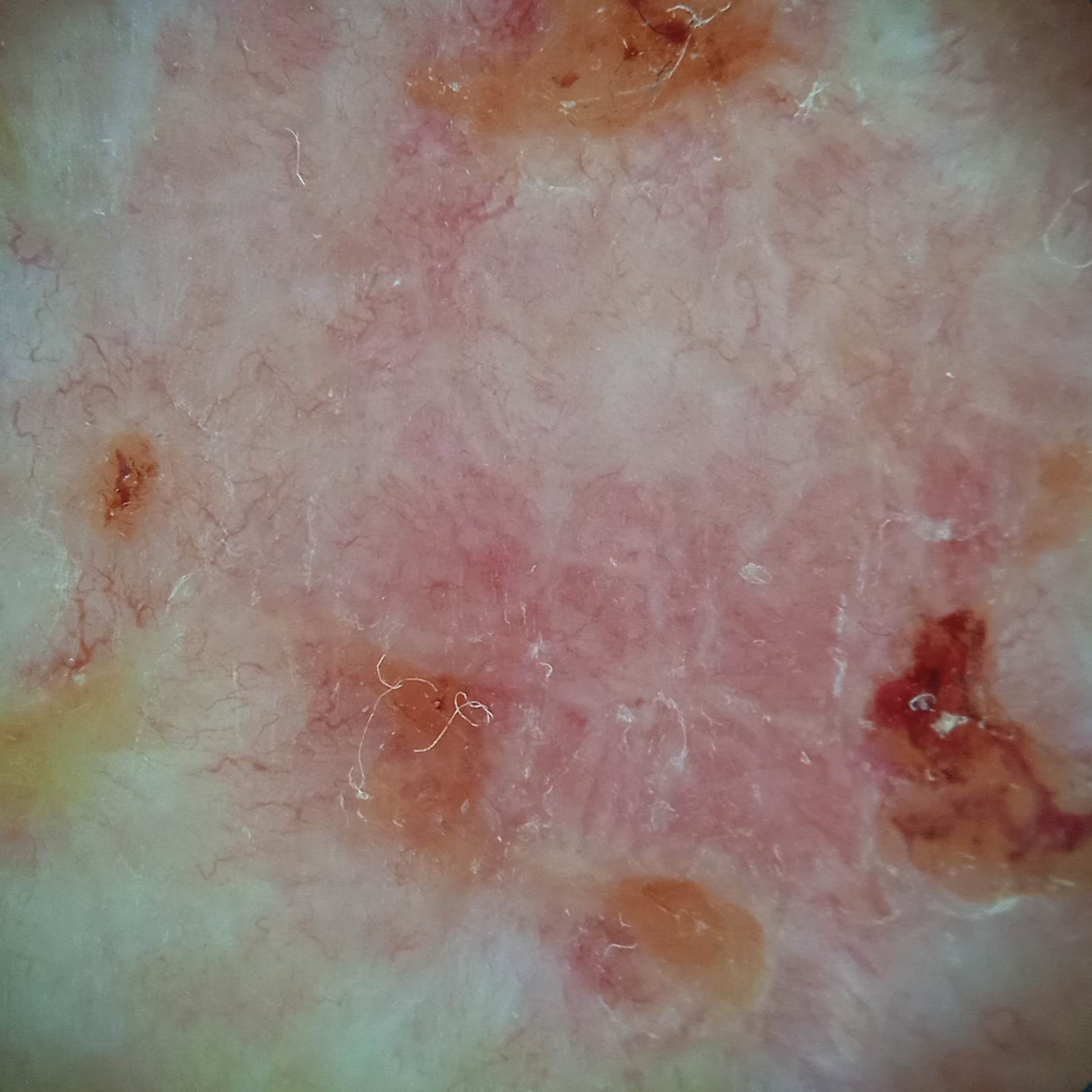mole_burden: few melanocytic nevi overall
risk_factors:
  positive:
    - a personal history of cancer
    - a family history of skin cancer
referral: clinical suspicion of basal cell carcinoma
patient:
  age: 81
  sex: male
image: dermoscopic image
lesion_location: the back
lesion_size:
  diameter_mm: 12.6
diagnosis:
  name: basal cell carcinoma
  malignancy: malignant
  procedure: excision
  tumor_thickness_mm: 3.0